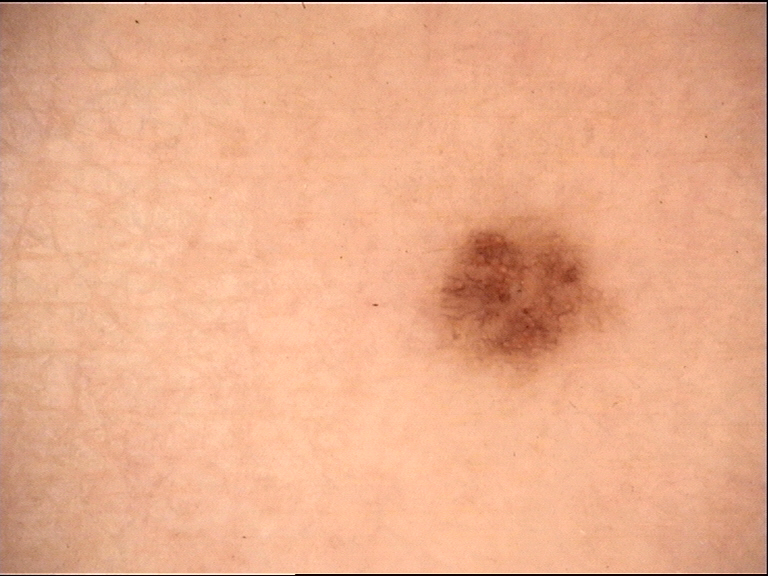modality — dermatoscopy
label — dysplastic junctional nevus (expert consensus)